The condition has been present for one to four weeks. The lesion is associated with itching, bothersome appearance and burning. The photograph is a close-up of the affected area. Skin tone: non-clinician graders estimated Monk skin tone scale 1 or 2. The lesion involves the top or side of the foot. Texture is reported as fluid-filled and raised or bumpy. The patient also reports shortness of breath.
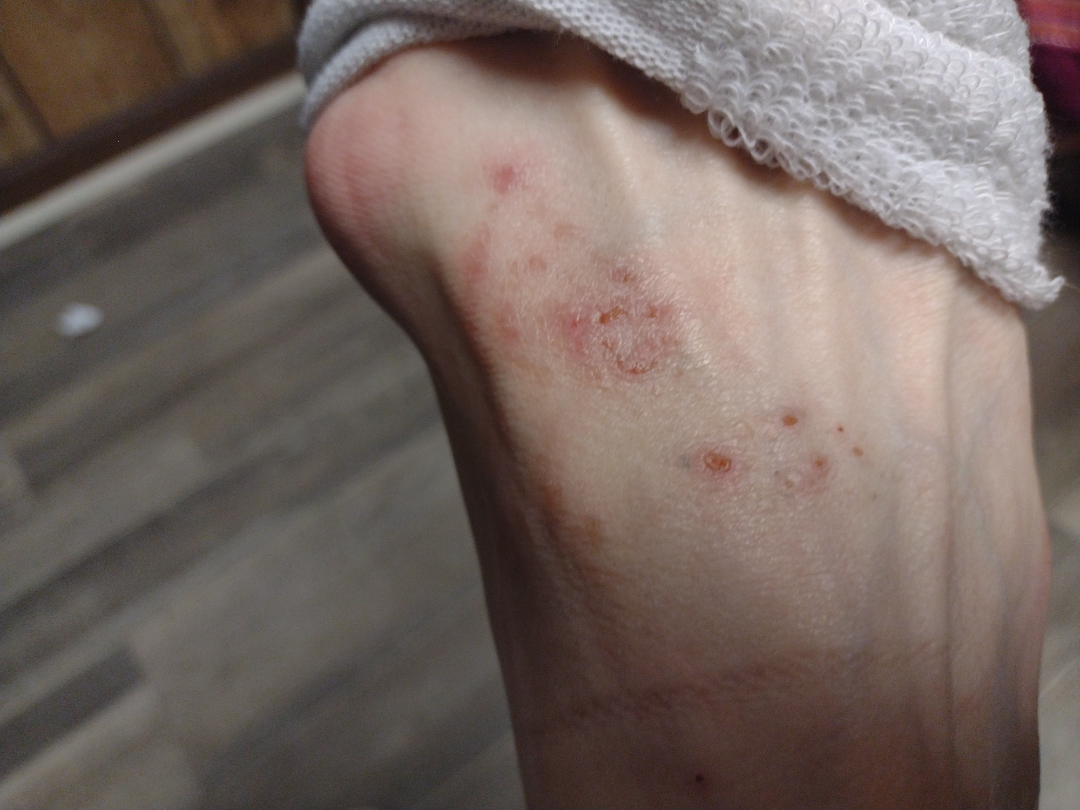| field | value |
|---|---|
| assessment | ungradable on photographic review |